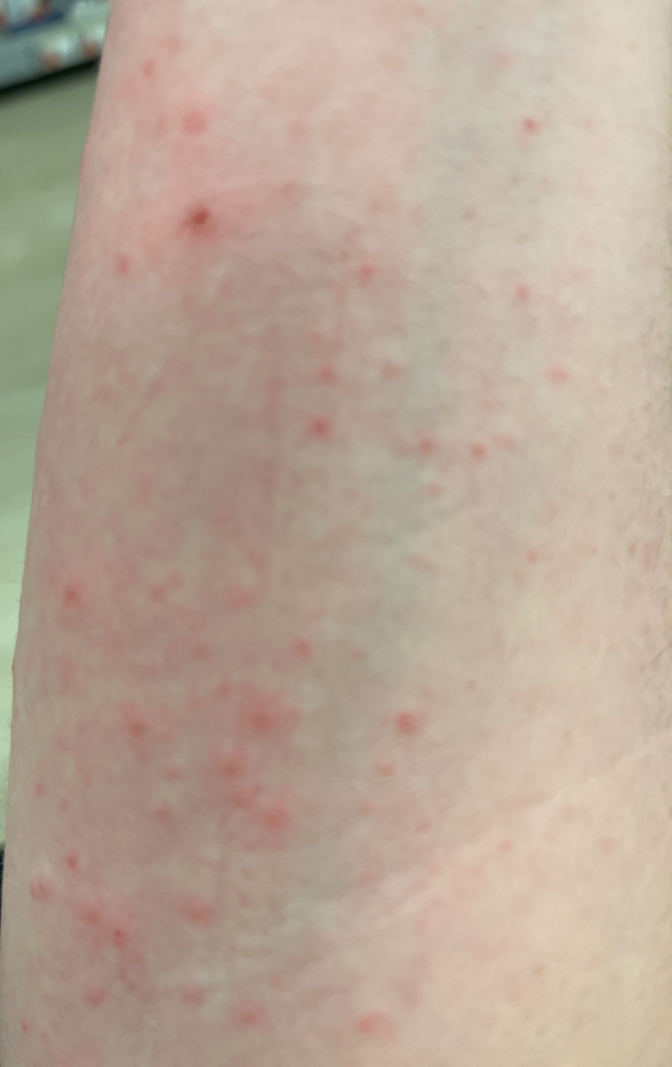| field | value |
|---|---|
| framing | close-up |
| differential | one reviewing dermatologist: most consistent with Allergic Contact Dermatitis; with consideration of Folliculitis; also consider Keratosis pilaris |